The photograph is a close-up of the affected area · texture is reported as raised or bumpy · the affected area is the leg:
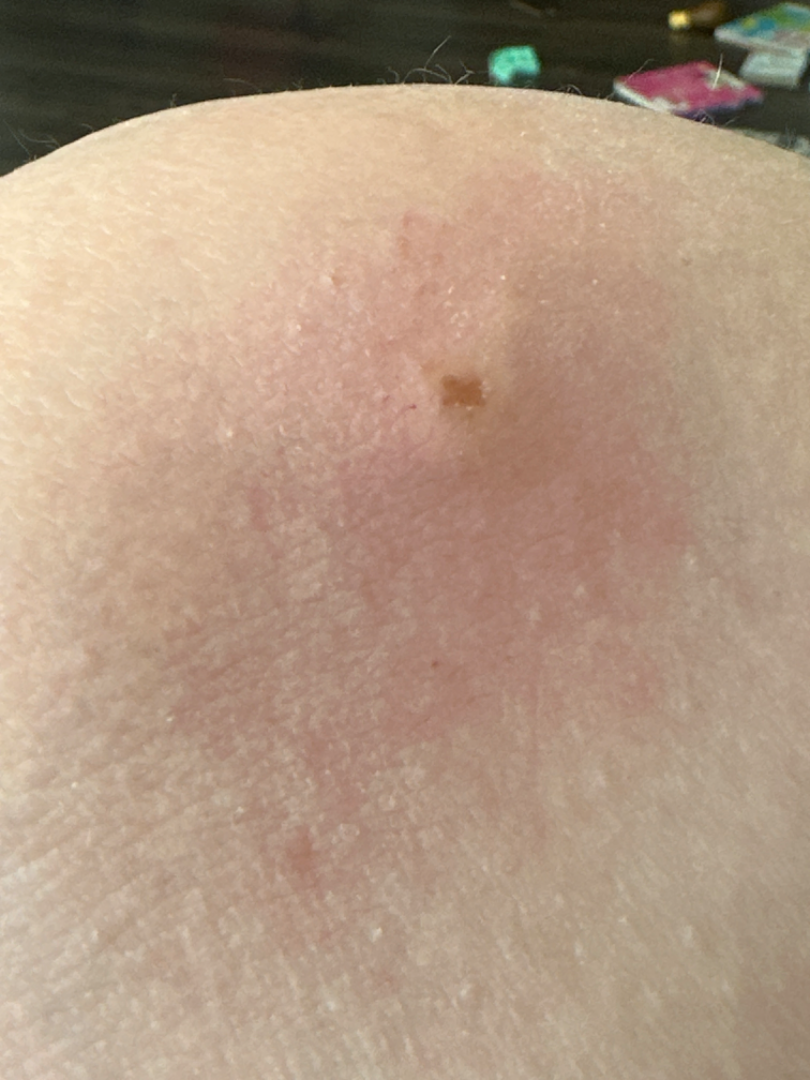* differential · most likely Insect Bite; possibly Abscess